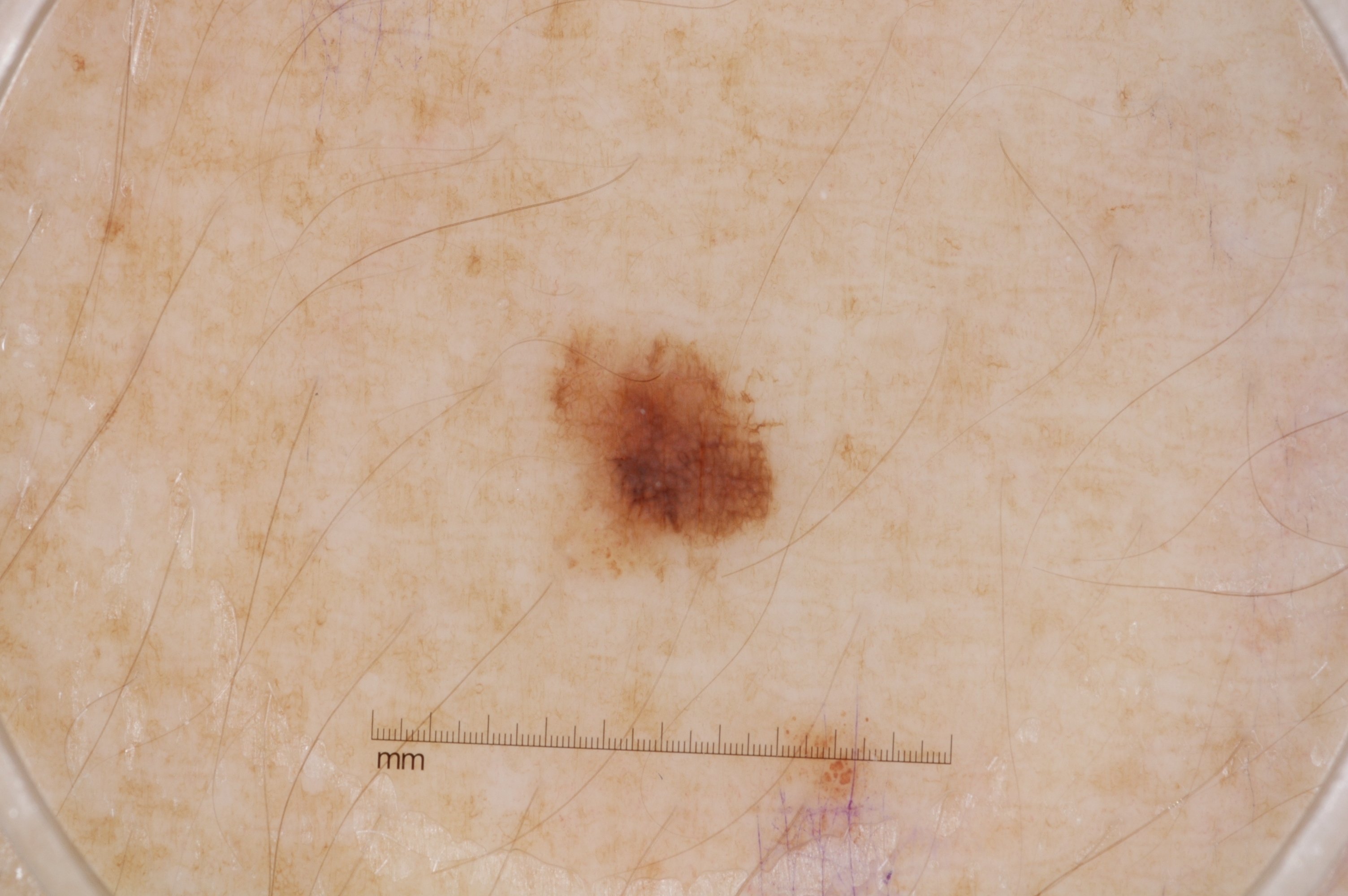| field | value |
|---|---|
| modality | dermoscopy |
| bounding box | x1=558, y1=336, x2=769, y2=567 |
| dermoscopic pattern | pigment network; absent: streaks, milia-like cysts, and negative network |
| lesion extent | small |
| impression | a melanocytic nevus, a benign skin lesion |